The contributor is a female aged 18–29; the photo was captured at an angle; located on the arm, sole of the foot, palm and leg.
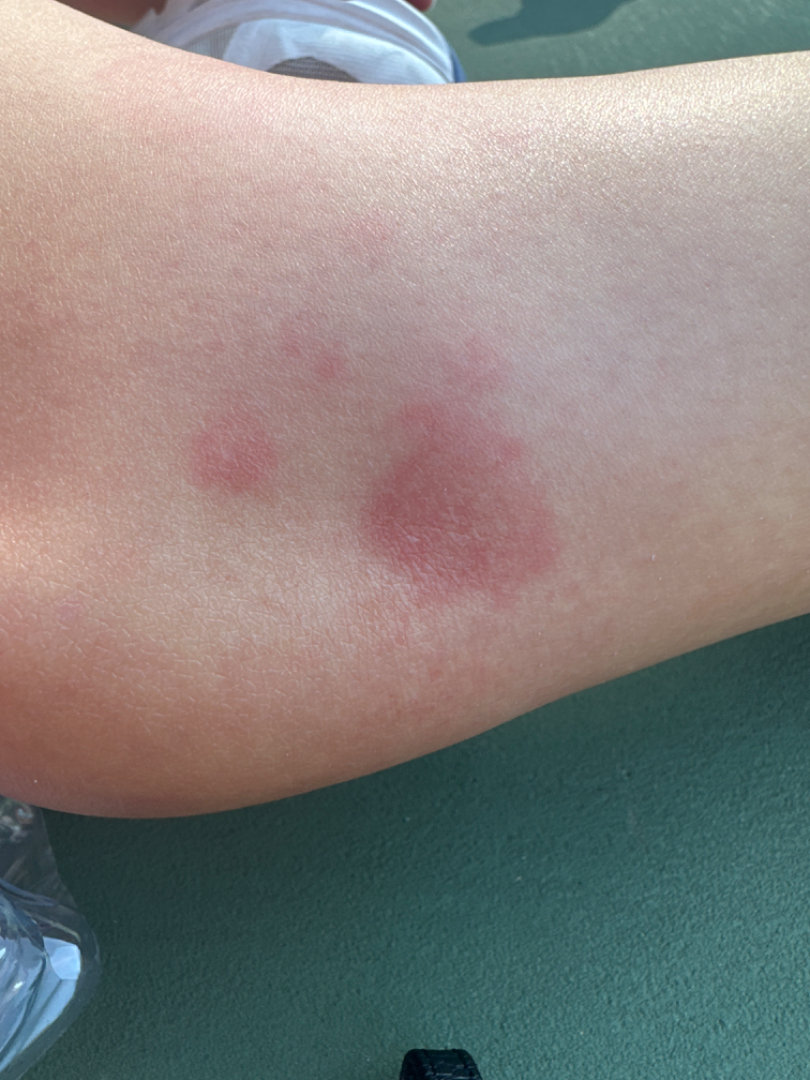Texture is reported as raised or bumpy. The lesion is associated with itching and bothersome appearance. Fitzpatrick phototype II. The patient also reports fatigue. Most consistent with Urticaria; the differential also includes Eczema; also raised was Granuloma annulare.